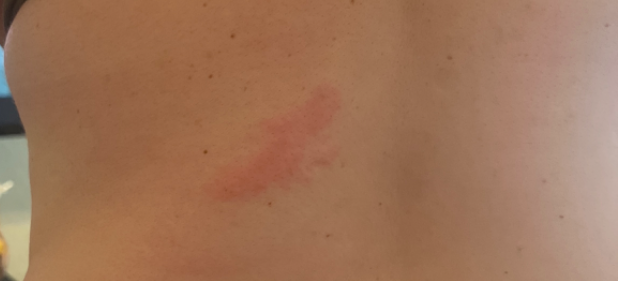| feature | finding |
|---|---|
| assessment | ungradable on photographic review |
| shot type | close-up |
| affected area | back of the torso |